A dermoscopy image of a single skin lesion: 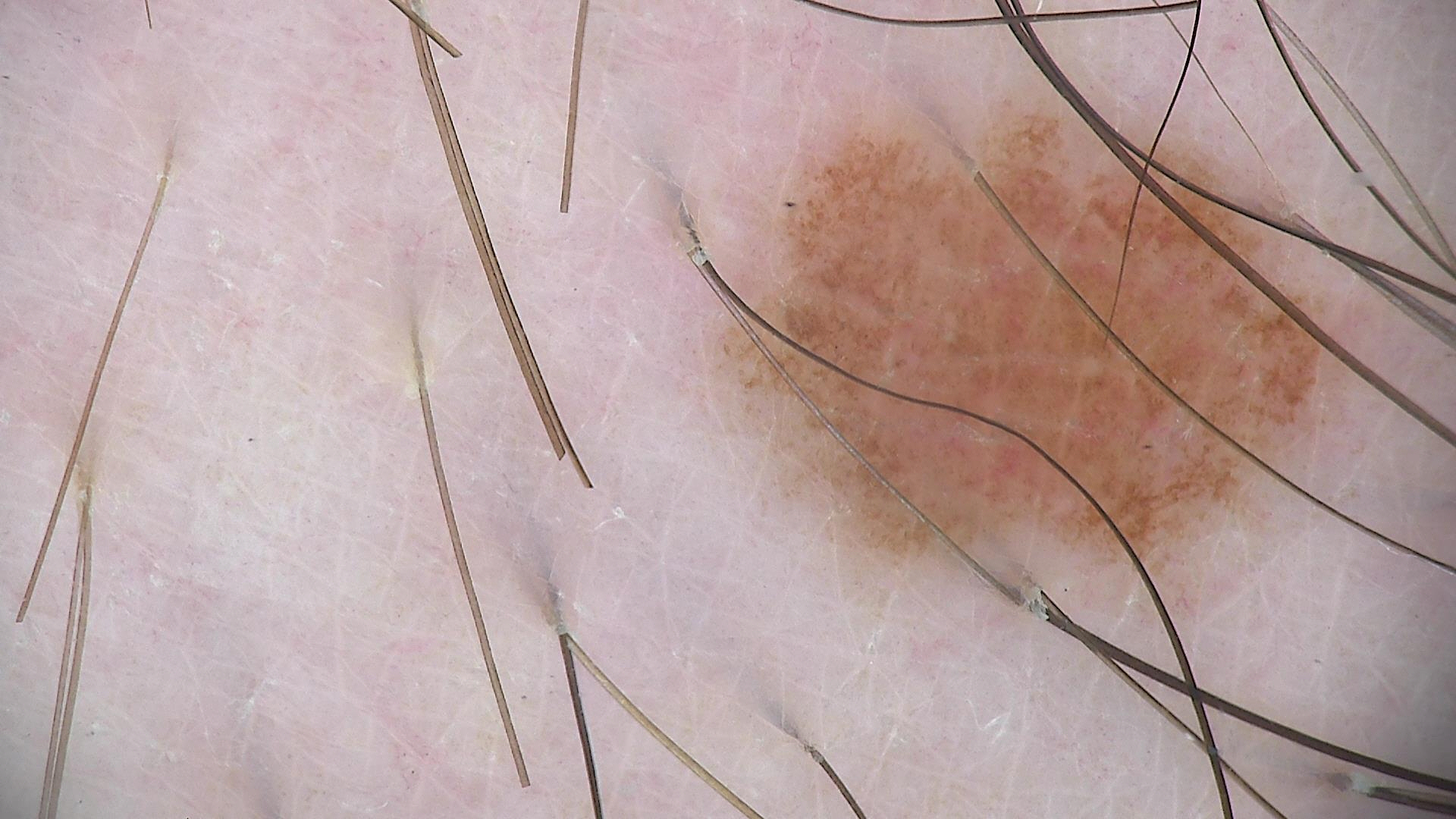The diagnosis was a dysplastic junctional nevus.